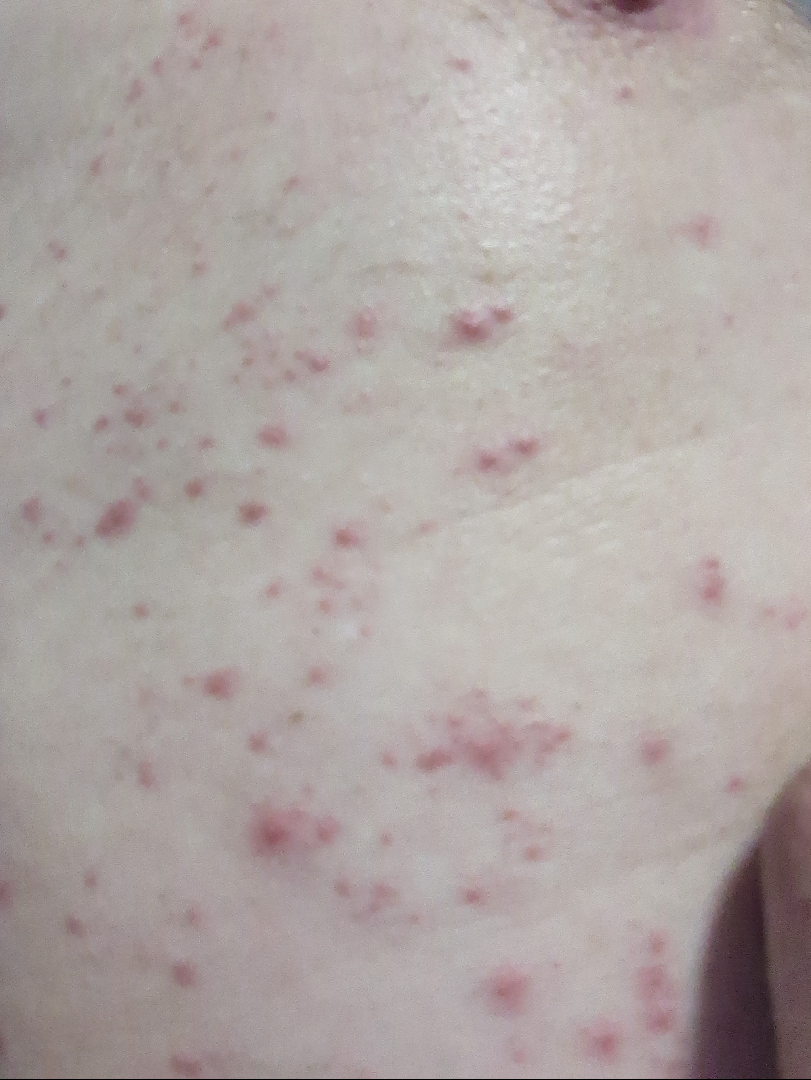assessment: indeterminate, skin tone: non-clinician graders estimated 2 on the Monk skin tone scale, anatomic site: back of the torso and front of the torso, onset: about one day, photo taken: close-up, constitutional symptoms: joint pain and fatigue.